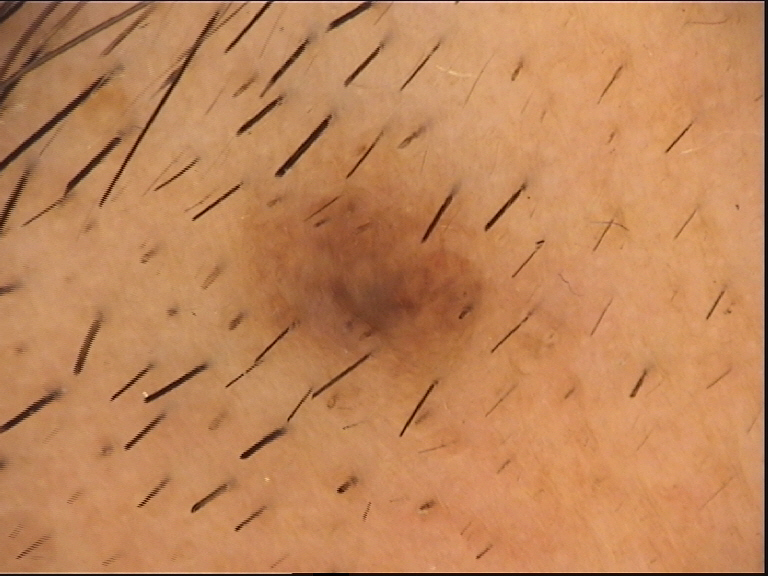image type — dermatoscopy; classification — banal; label — compound nevus (expert consensus).